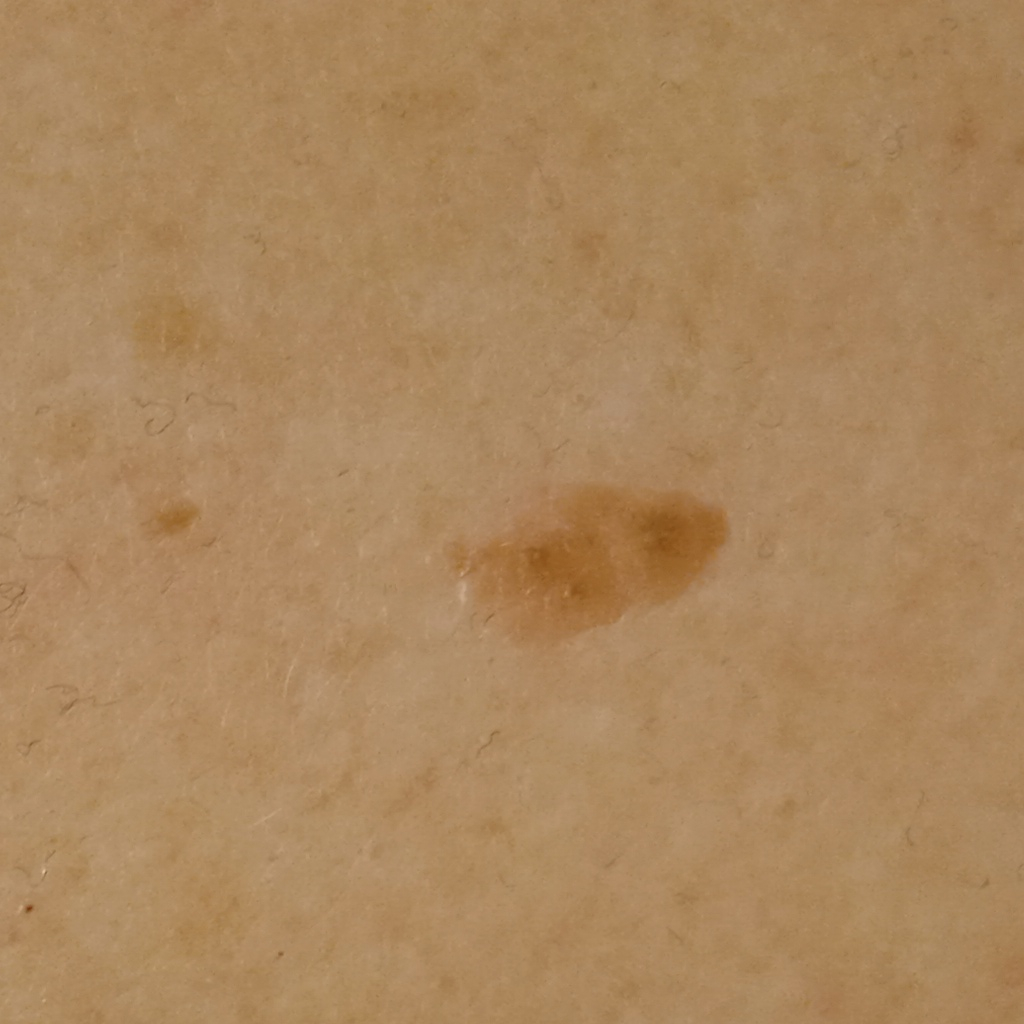  mole_burden: a moderate number of melanocytic nevi
  image: clinical photo
  patient:
    age: 59
    sex: female
  sun_reaction: skin reddens with sun exposure
  referral: research study (no referral diagnosis)
  lesion_location: the torso
  lesion_size:
    diameter_mm: 9.1
  diagnosis:
    name: seborrheic keratosis
    malignancy: benign